A skin lesion imaged with a dermatoscope: 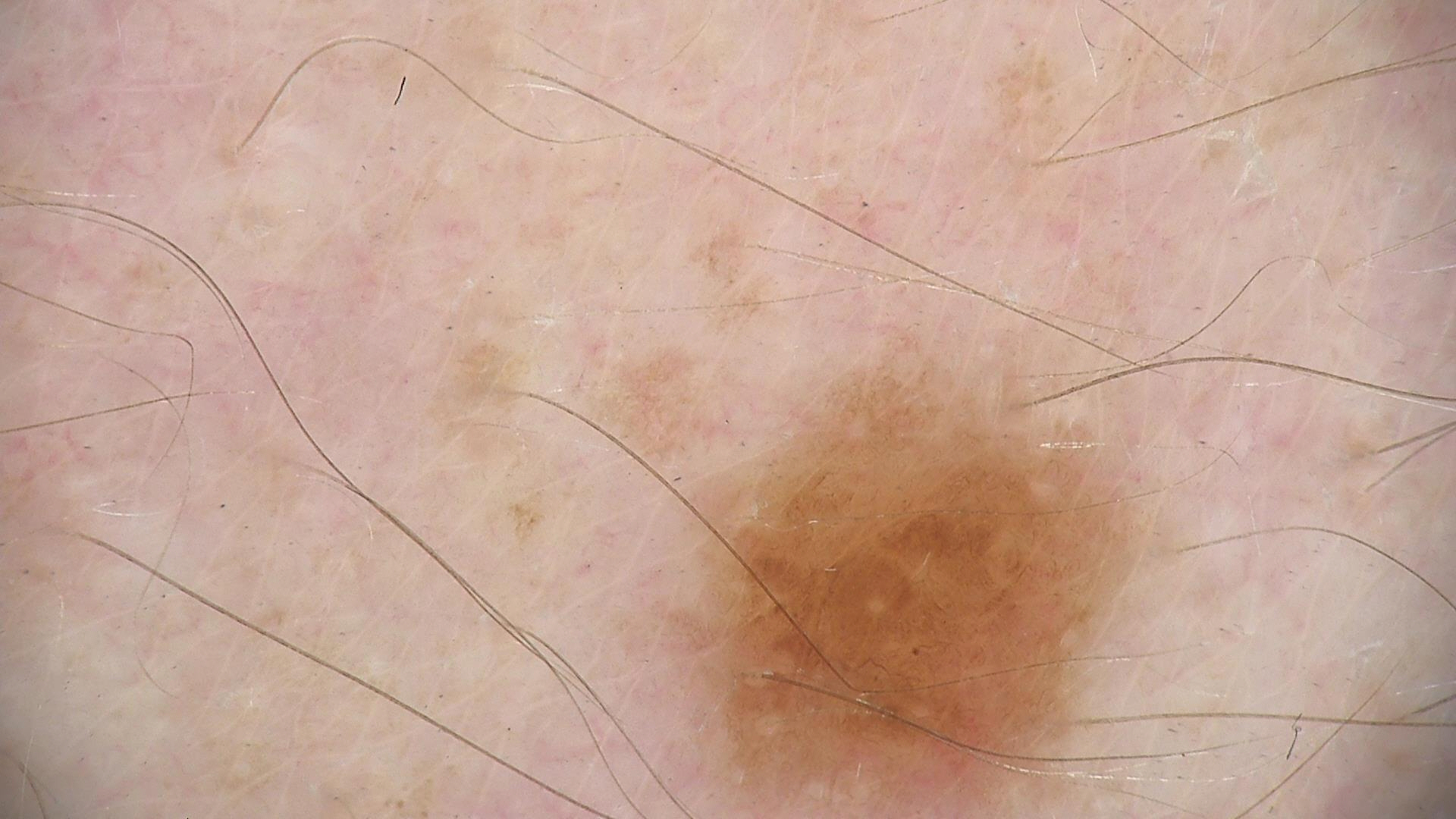Impression:
The diagnostic label was a benign lesion — a dysplastic junctional nevus.